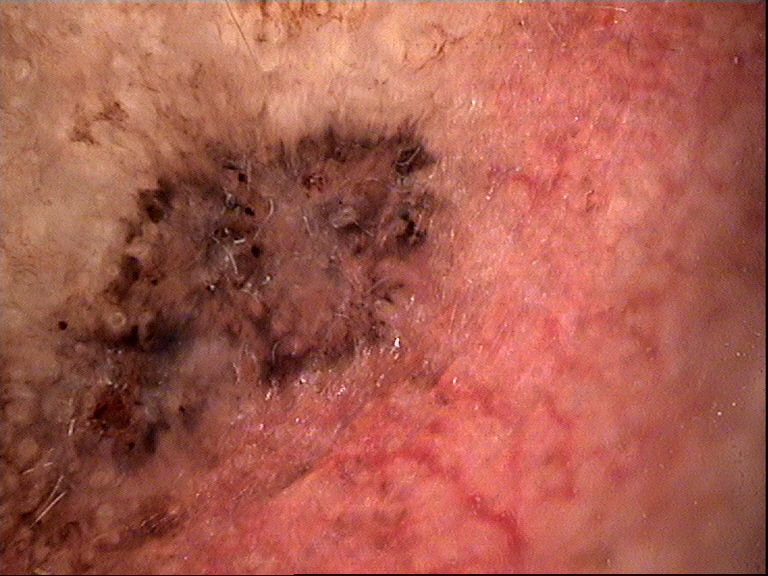A skin lesion imaged with a dermatoscope.
Histopathology confirmed a keratinocytic lesion — a basal cell carcinoma.